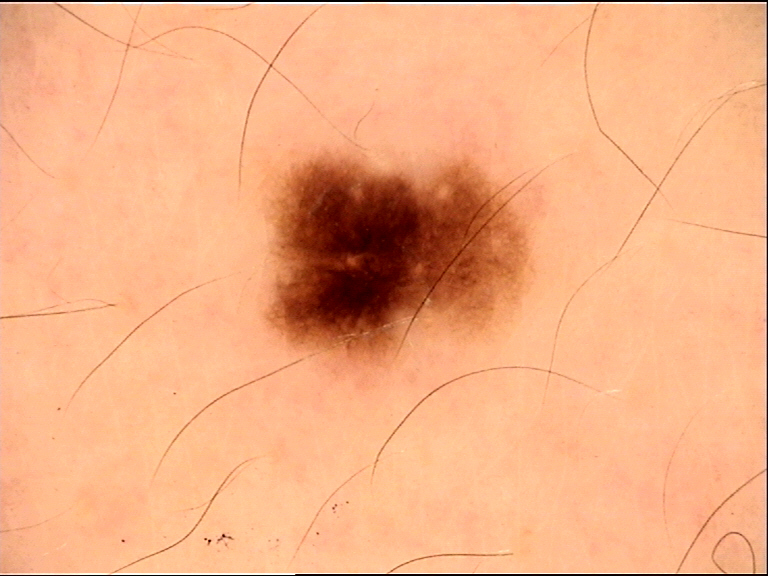category: banal, diagnostic label: junctional nevus (expert consensus).